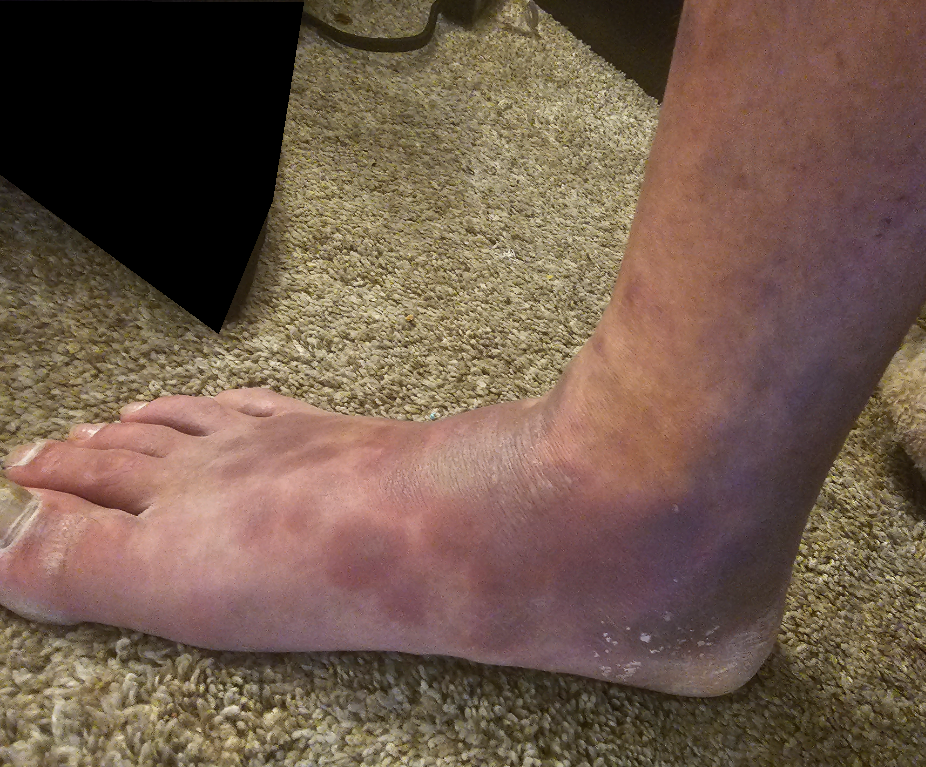Q: What conditions are considered?
A: Lichen Simplex Chronicus, Eczema and Psoriasis were each considered, in no particular order; less likely is Drug Rash; lower on the differential is Erythema multiforme; a remote consideration is Acute and chronic dermatitis; less probable is Stasis Dermatitis; a more distant consideration is Lichen planus/lichenoid eruption